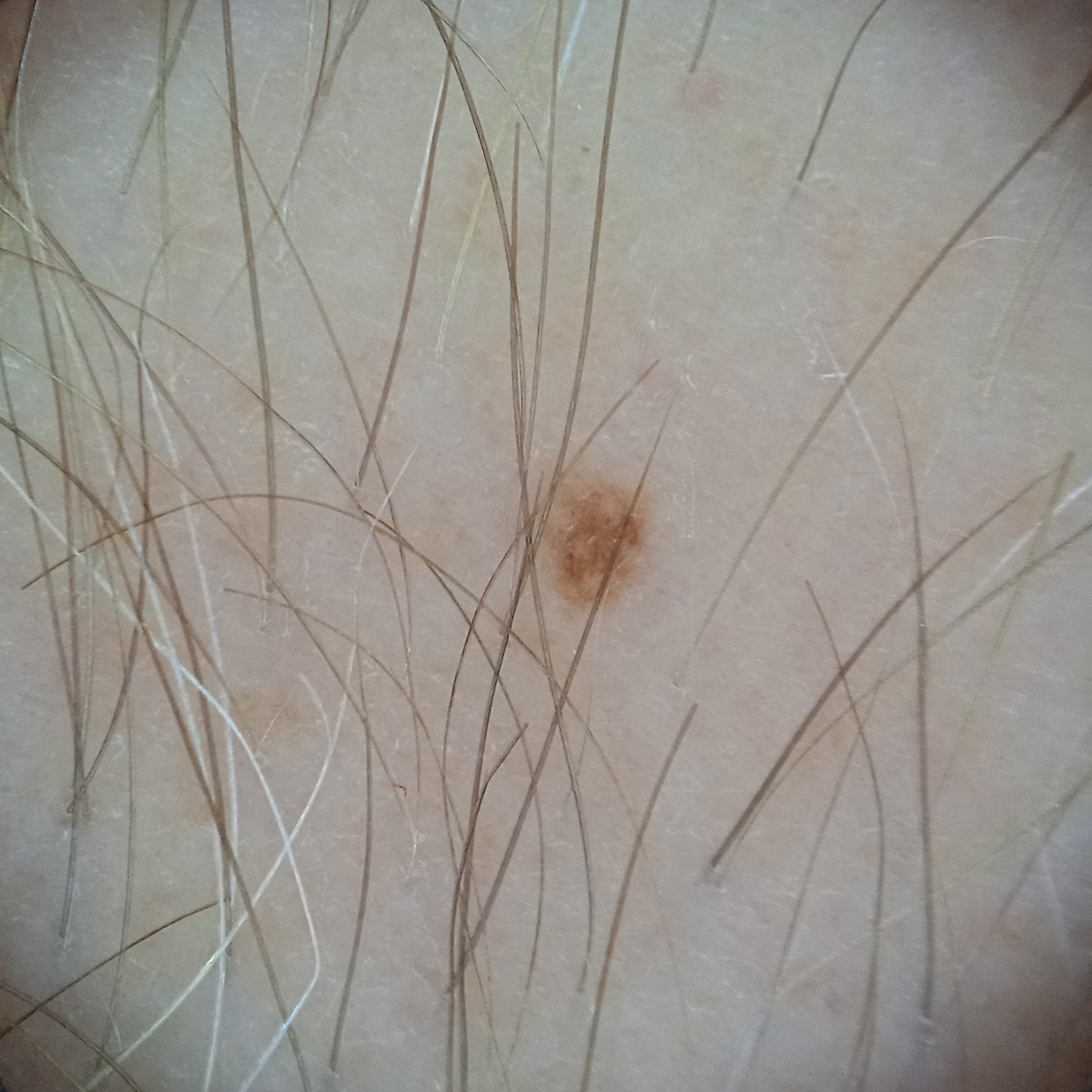Imaged for a research study, with no referral diagnosis recorded. A male subject aged 60. The lesion is on an arm. Measuring roughly 1.5 mm. The consensus diagnosis for this lesion was a melanocytic nevus.